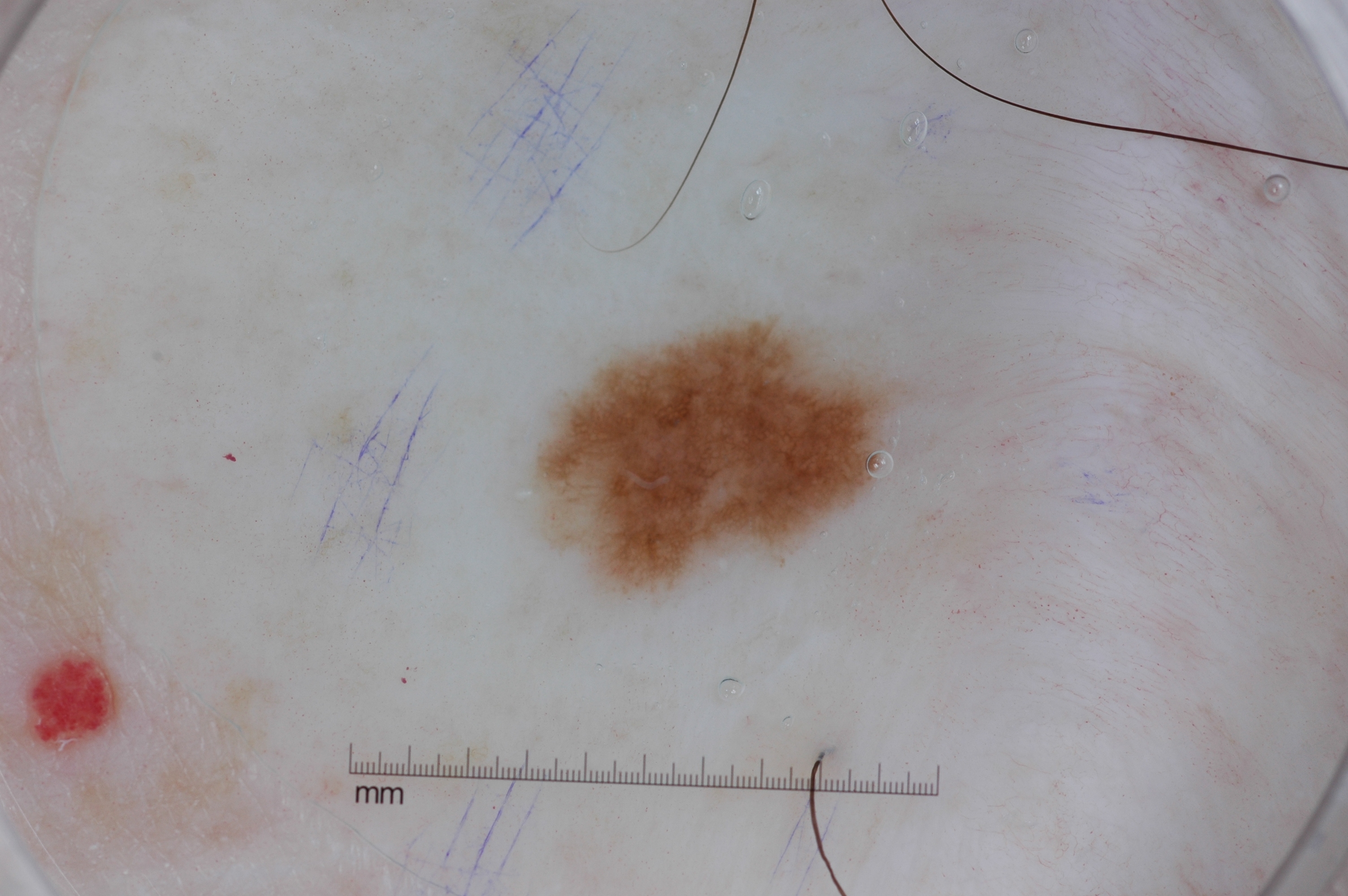{
  "image": {
    "modality": "dermoscopy"
  },
  "patient": {
    "sex": "male",
    "age_approx": 75
  },
  "dermoscopic_features": {
    "present": [
      "pigment network"
    ],
    "absent": [
      "negative network",
      "streaks",
      "milia-like cysts"
    ]
  },
  "lesion_extent": "small",
  "lesion_location": {
    "bbox_xyxy": [
      537,
      322,
      885,
      588
    ]
  },
  "diagnosis": {
    "name": "melanocytic nevus",
    "malignancy": "benign",
    "lineage": "melanocytic",
    "provenance": "clinical"
  }
}